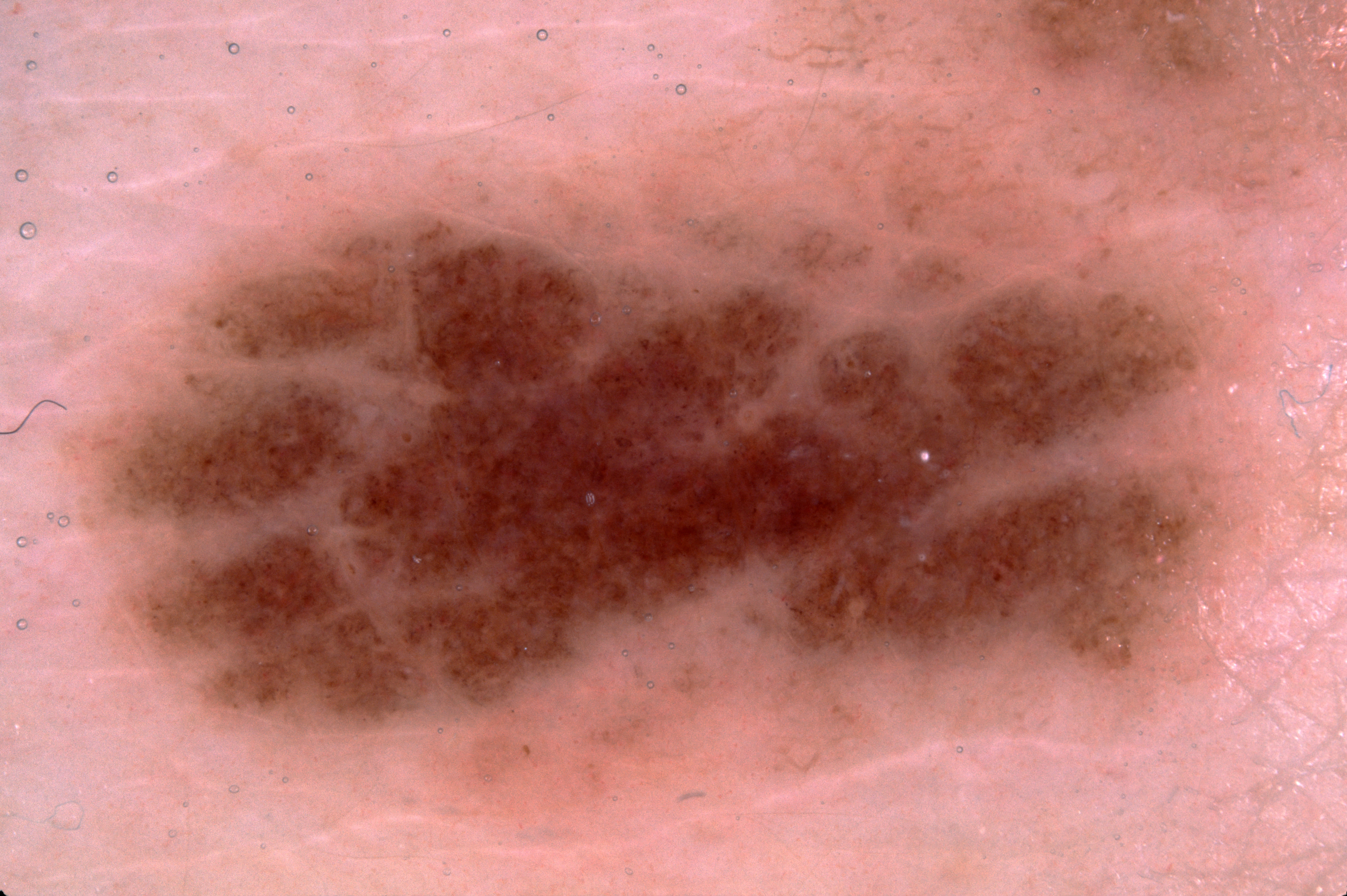The patient is a female aged 38 to 42. A dermoscopy image of a single skin lesion. Part of the lesion extends beyond the imaged area. Dermoscopy demonstrates no milia-like cysts, negative network, pigment network, or streaks. In (x1, y1, x2, y2) order, the lesion's extent is bbox(57, 0, 1346, 826). The lesion takes up about 61% of the image. The lesion was assessed as a melanocytic nevus.